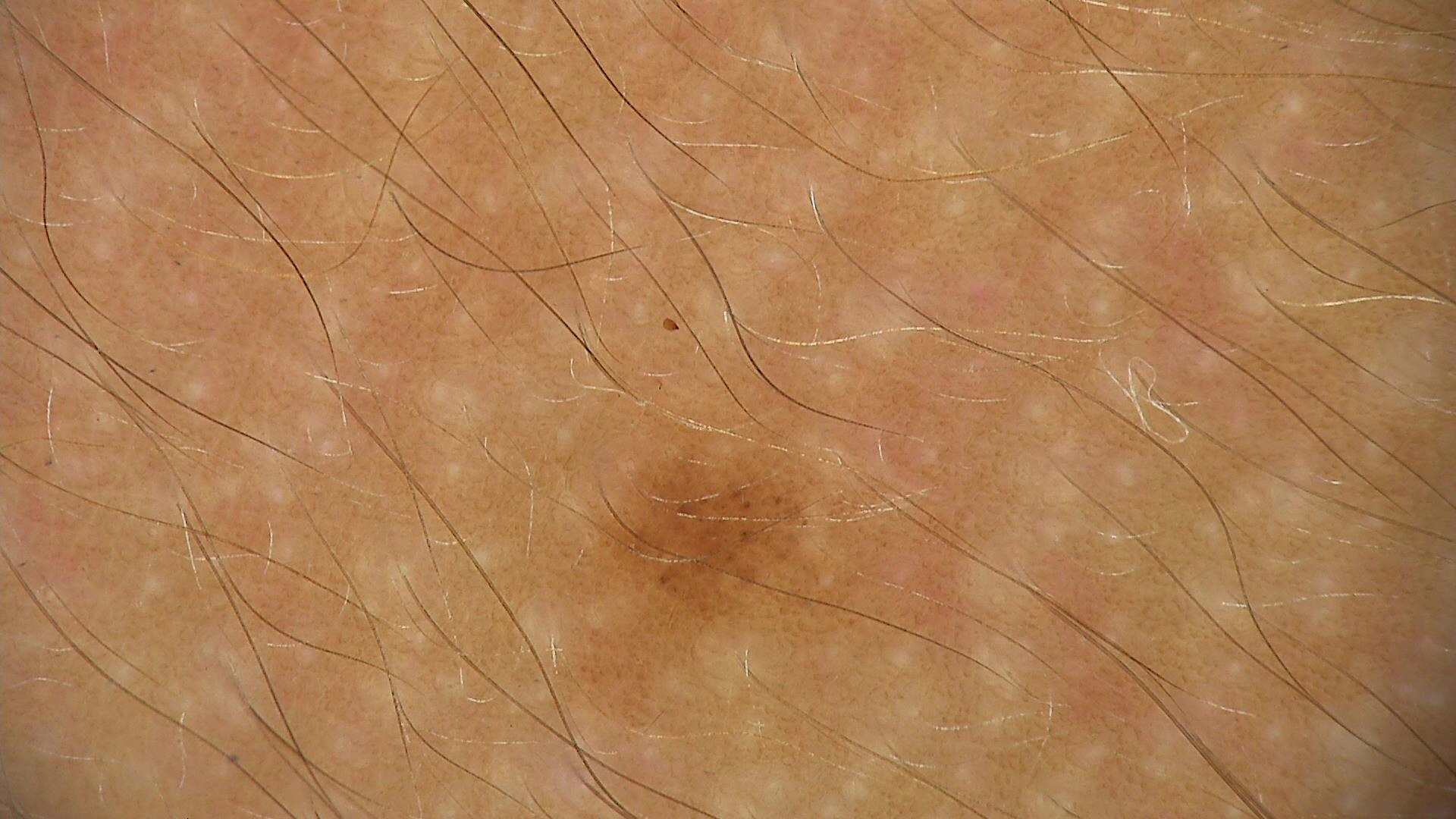Diagnosed as a dysplastic junctional nevus.